Male patient, age 40–49 · the patient reported no systemic symptoms · reported duration is less than one week · the arm and leg are involved · this image was taken at a distance:
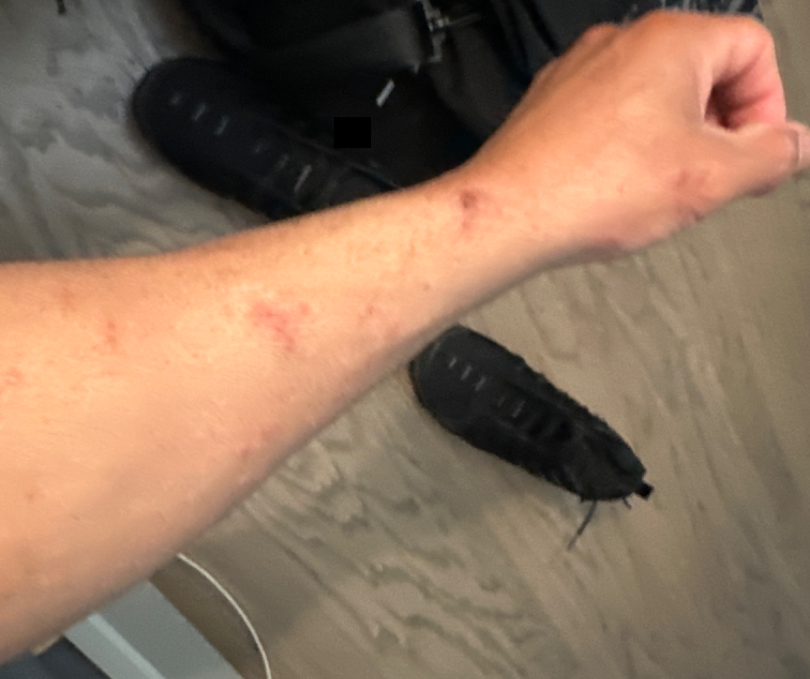Notes:
* assessment: most consistent with Folliculitis; also consider Allergic Contact Dermatitis; less probable is Localized skin infection